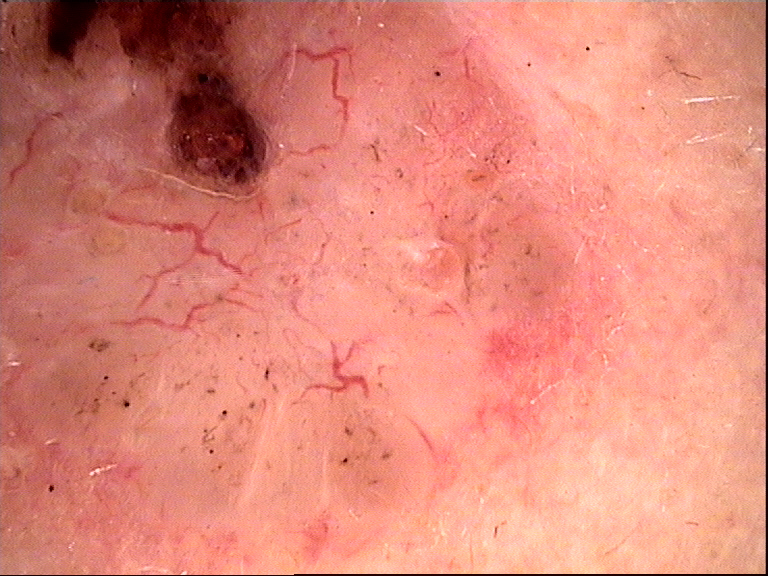Q: What is the imaging modality?
A: dermatoscopy
Q: What kind of lesion is this?
A: keratinocytic
Q: What did the workup show?
A: basal cell carcinoma (biopsy-proven)